Dermoscopy of a skin lesion. A male subject, roughly 45 years of age:
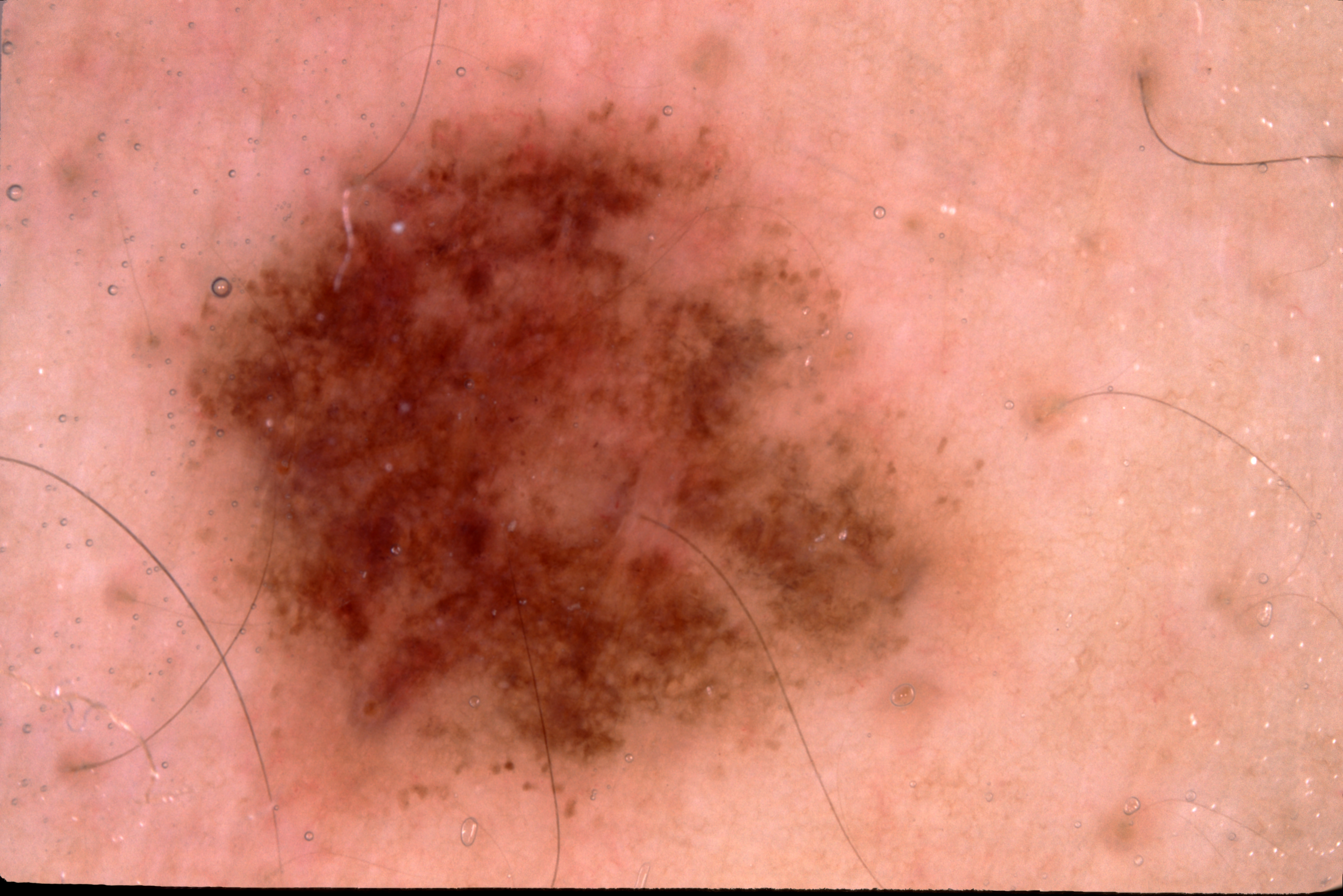The dermoscopic pattern shows milia-like cysts and pigment network. The lesion is bounded by left=126, top=87, right=999, bottom=867. Diagnosed as a melanocytic nevus.